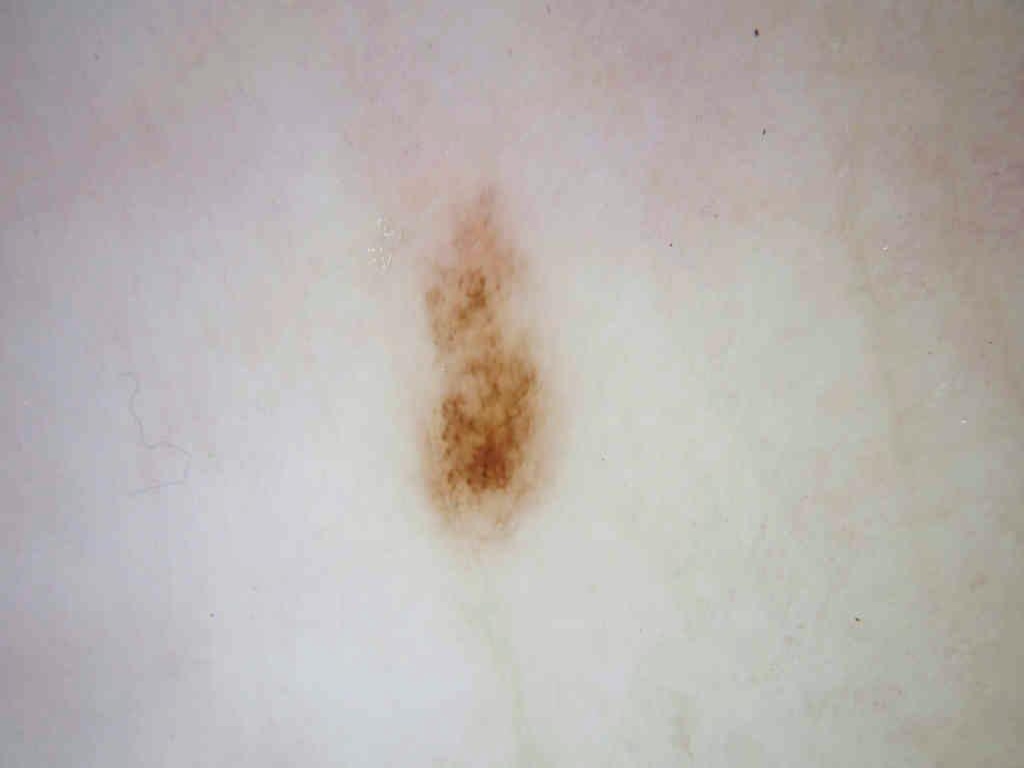| field | value |
|---|---|
| image type | dermatoscopic image of a skin lesion |
| location | x1=419, y1=185, x2=552, y2=530 |
| dermoscopic findings | pigment network; absent: milia-like cysts, globules, streaks, and negative network |
| size | ~4% of the field |
| diagnosis | a melanocytic nevus |